Located on the back of the hand and palm. Present for three to twelve months. The contributor is 18–29, female. An image taken at an angle. The patient reports the lesion is rough or flaky. Skin tone: FST I. The patient also reports fatigue and shortness of breath. The patient considered this a rash. Symptoms reported: enlargement, burning, pain and itching — 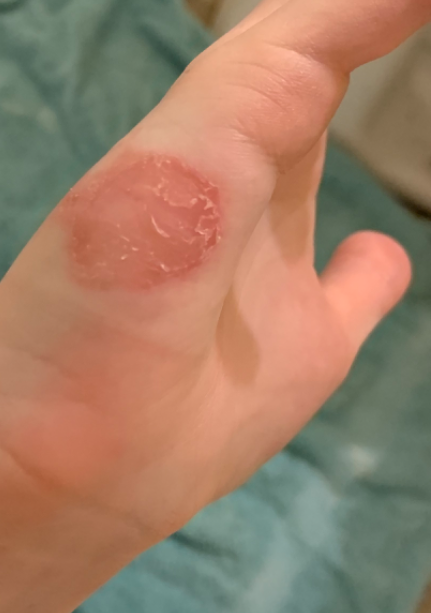impression: favoring Psoriasis; an alternative is Irritant Contact Dermatitis; less likely is Tinea; a more distant consideration is Eczema; less probable is Burn erythema of back of hand.